A dermatoscopic image of a skin lesion.
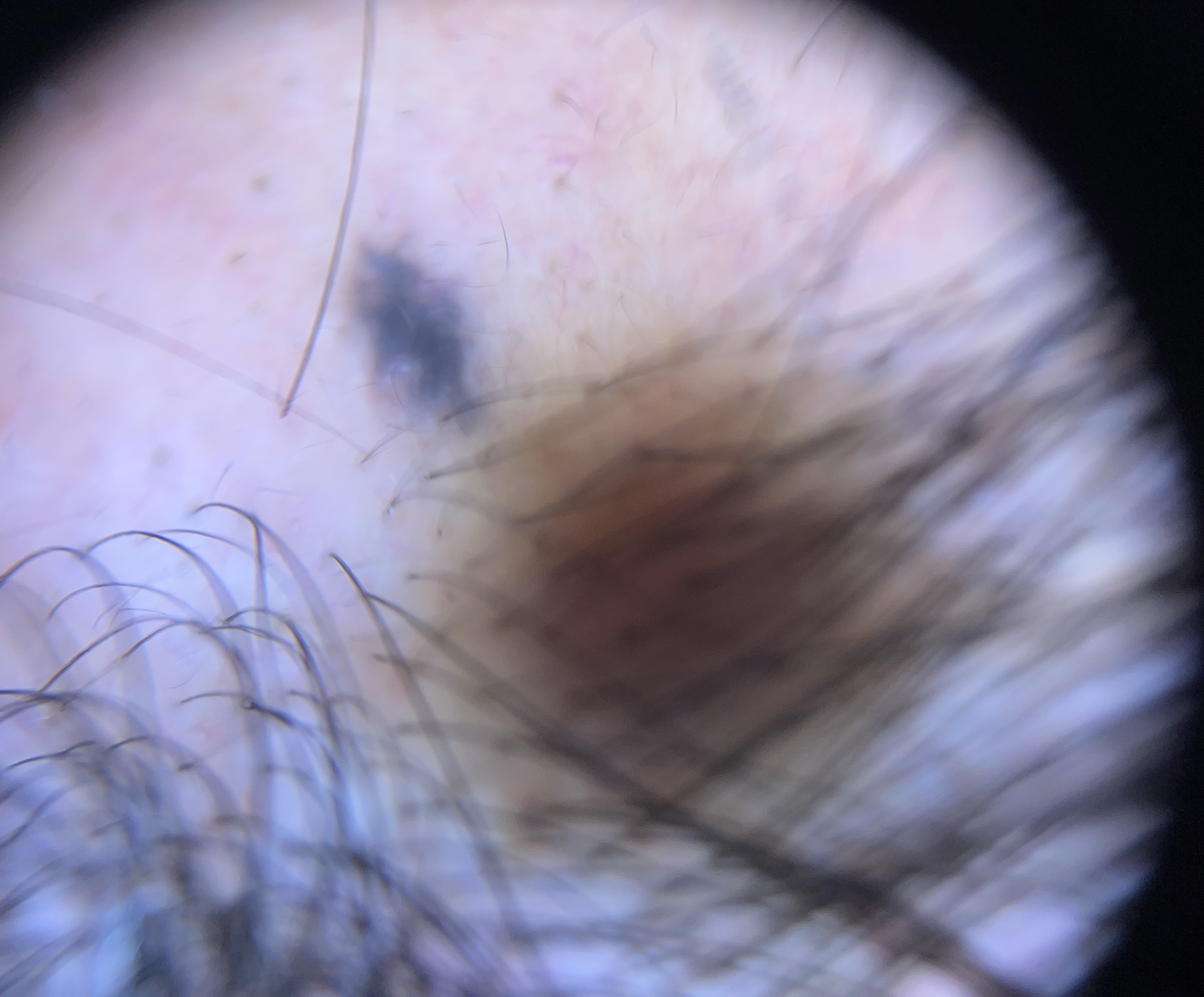Findings:
The morphology is that of a banal, dermal lesion.
Conclusion:
The diagnostic label was a blue nevus.